An image taken at an angle, texture is reported as raised or bumpy, the contributor notes burning and itching, the front of the torso is involved, no associated systemic symptoms reported, skin tone: human graders estimated Monk Skin Tone 1 or 2: 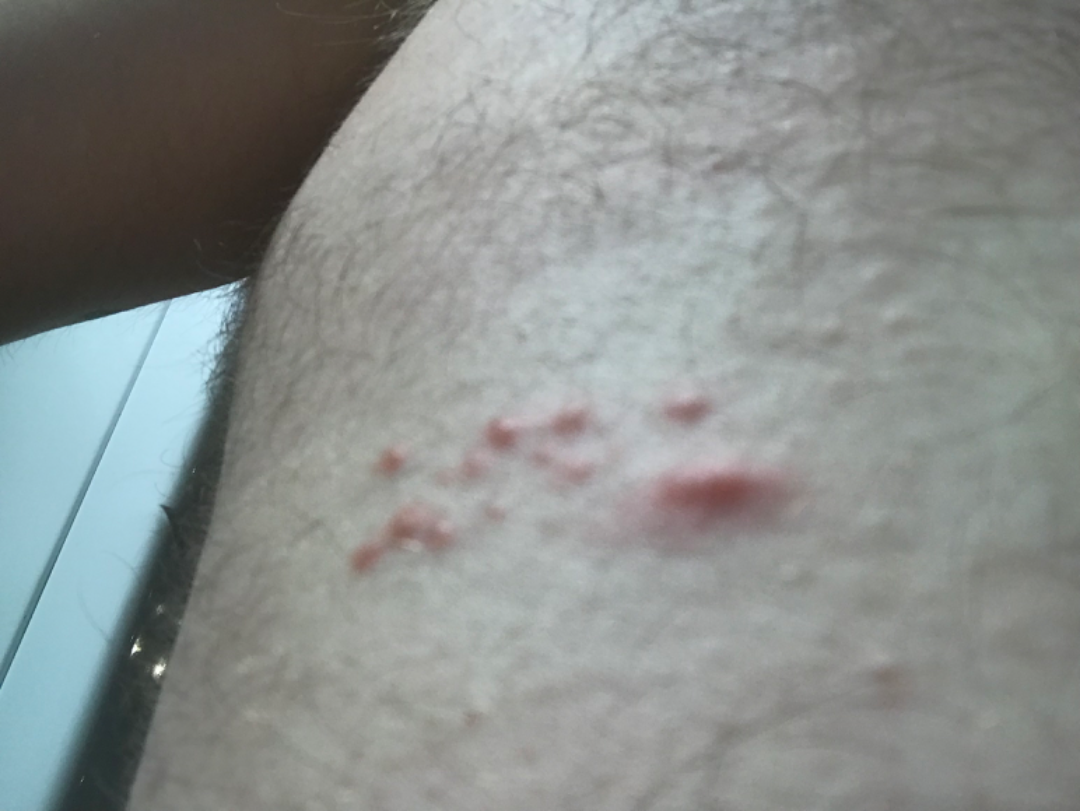The skin condition could not be confidently assessed from this image.